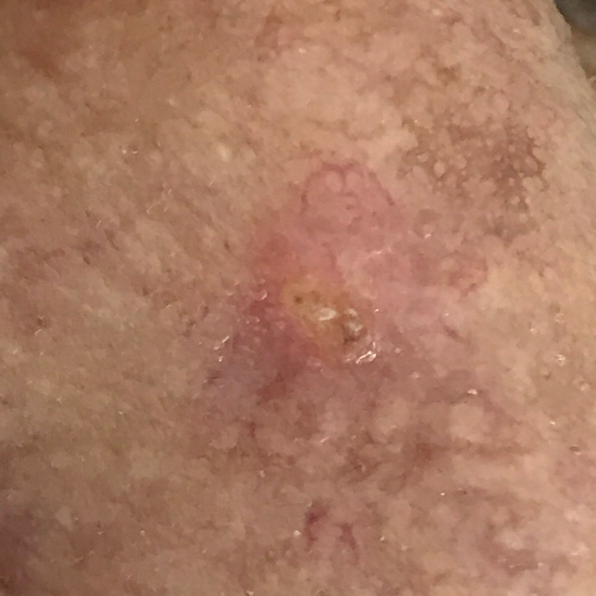History notes tobacco use. The patient is Fitzpatrick II. A male patient in their early 80s. The lesion measures approximately 5 × 4 mm. The biopsy diagnosis was a skin cancer — a basal cell carcinoma.